A dermoscopic image of a skin lesion: 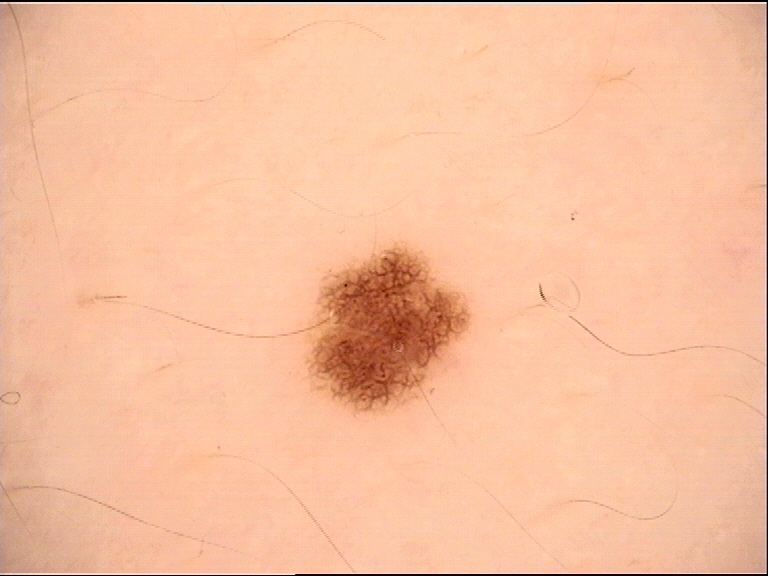diagnostic label: dysplastic junctional nevus (expert consensus)